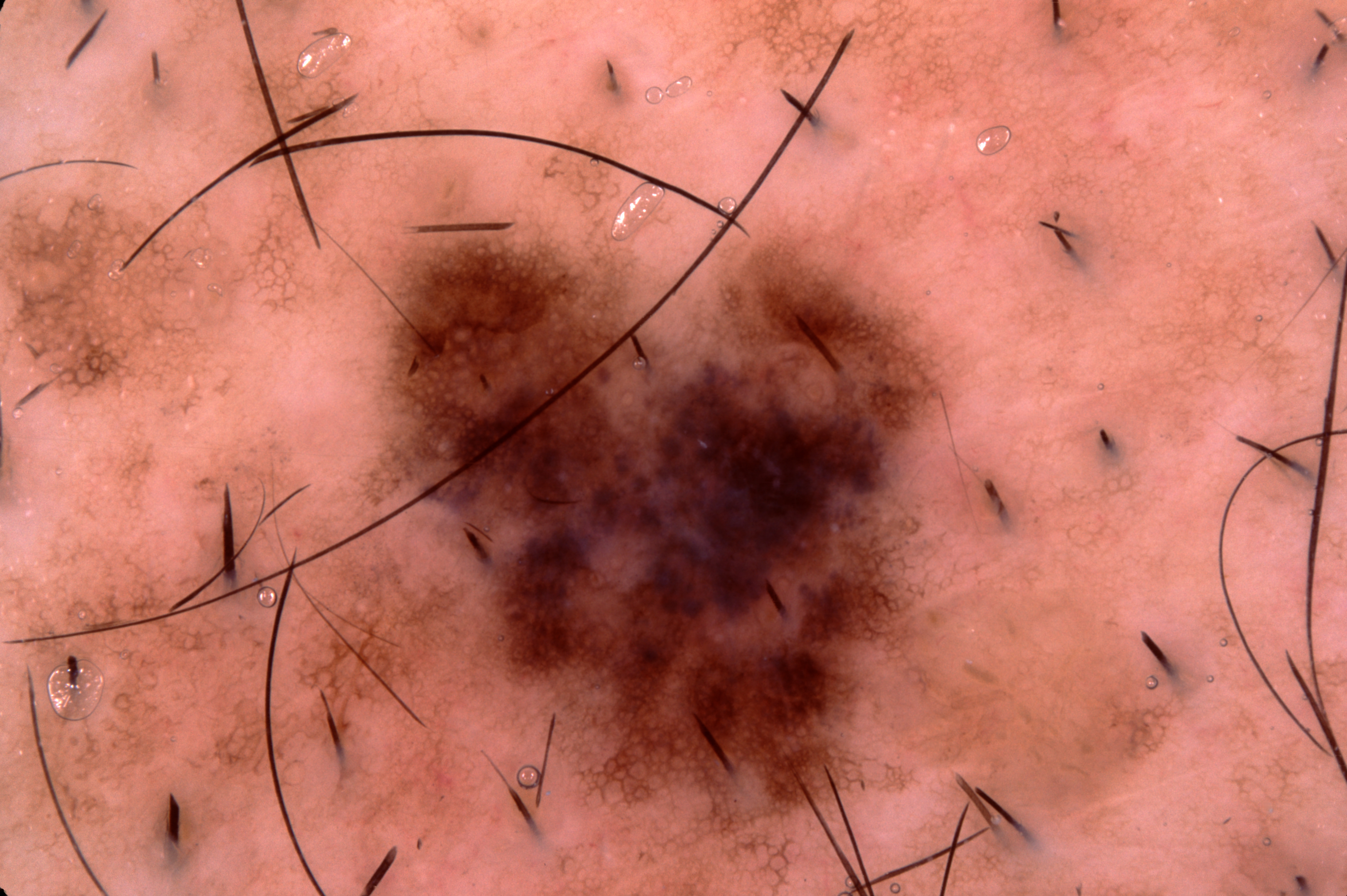{
  "image": {
    "modality": "dermoscopy"
  },
  "lesion_location": {
    "bbox_xyxy": [
      389,
      231,
      936,
      805
    ]
  },
  "diagnosis": {
    "name": "melanoma",
    "malignancy": "malignant",
    "lineage": "melanocytic",
    "provenance": "histopathology"
  }
}